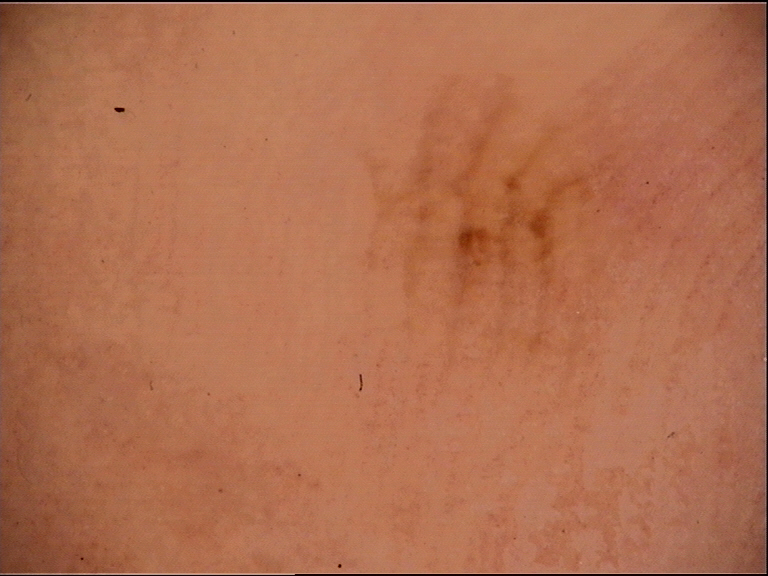assessment=acral dysplastic junctional nevus (expert consensus).